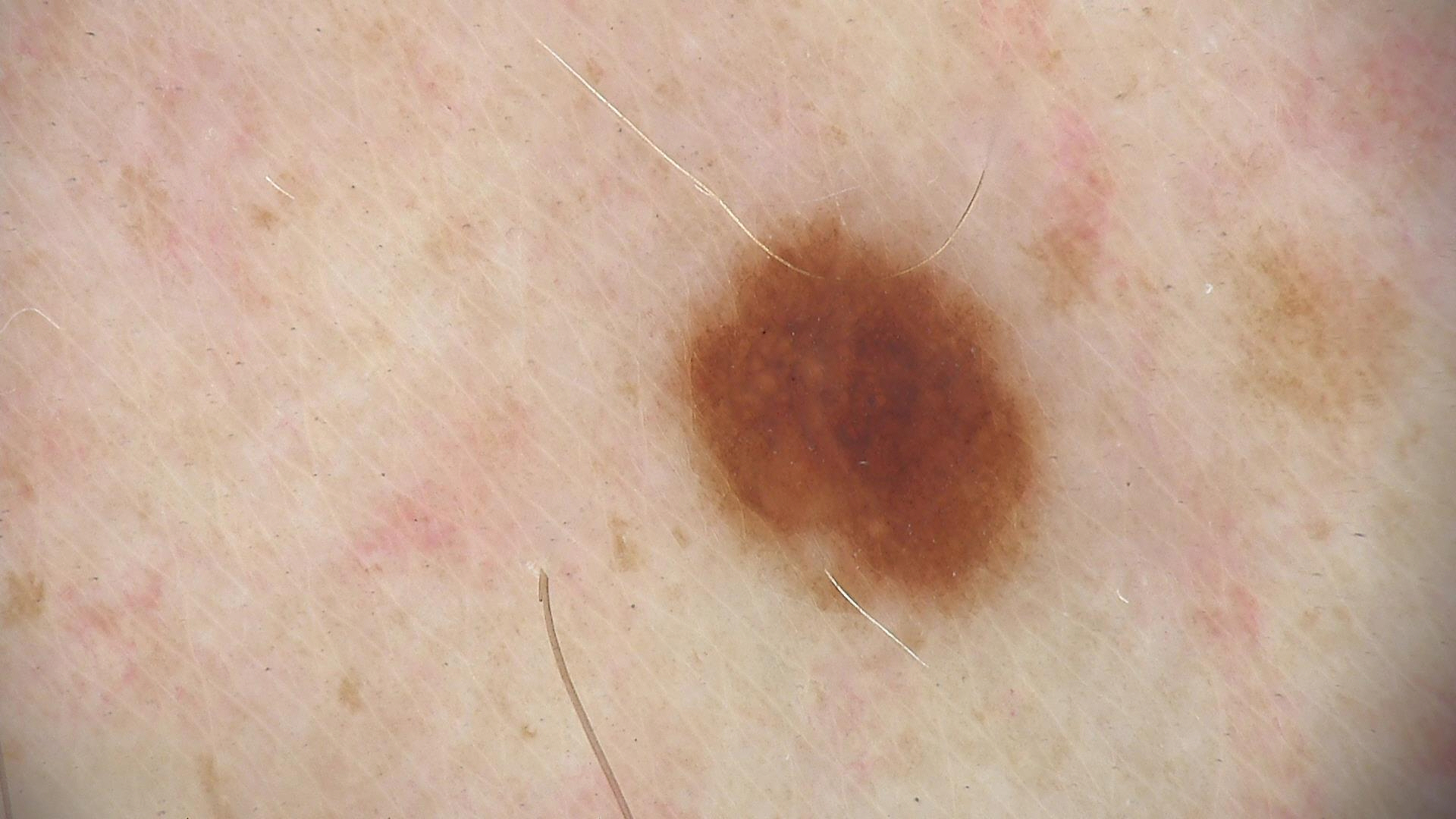Findings: A dermoscopic image of a skin lesion. Impression: Classified as a benign lesion — a dysplastic junctional nevus.